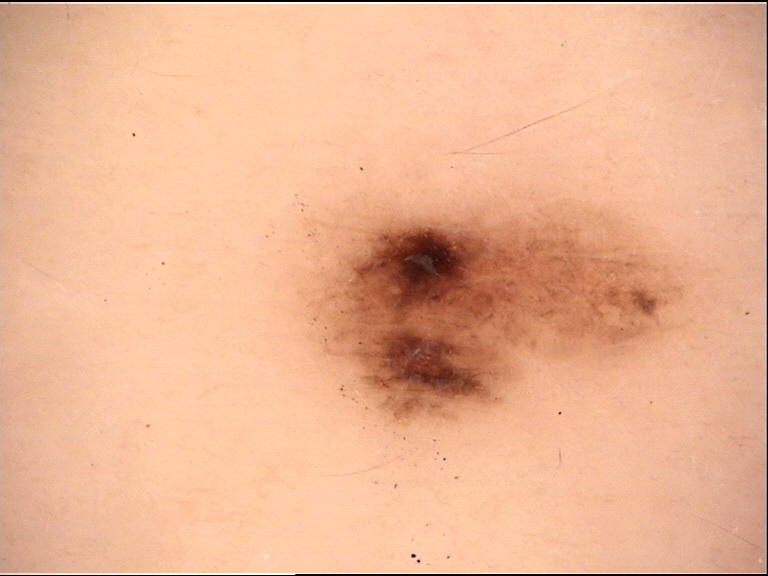Conclusion: The diagnosis was a dysplastic junctional nevus.